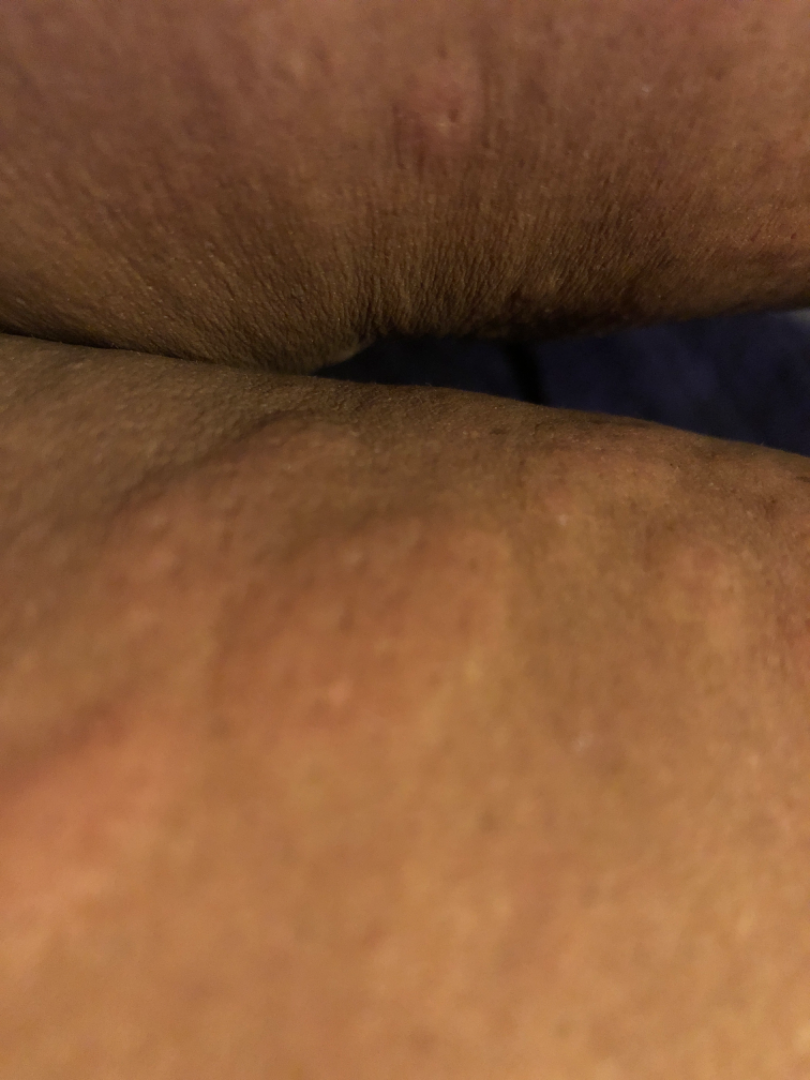{
  "duration": "three to twelve months",
  "body_site": [
    "head or neck",
    "front of the torso",
    "palm",
    "arm"
  ],
  "texture": "raised or bumpy",
  "systemic_symptoms": "none reported",
  "symptoms": "itching",
  "patient": "female, age 60–69",
  "patient_category": "a rash",
  "shot_type": "at an angle",
  "differential": {
    "Urticaria": 0.41,
    "Leukocytoclastic Vasculitis": 0.41,
    "Drug Rash": 0.18
  }
}